The patient says their skin reddens with sun exposure · the referring clinician suspected melanoma · a macroscopic clinical photograph of a skin lesion · a moderate number of moles by the patient's own estimate · a female subject aged 50 · the patient reports a personal history of skin cancer.
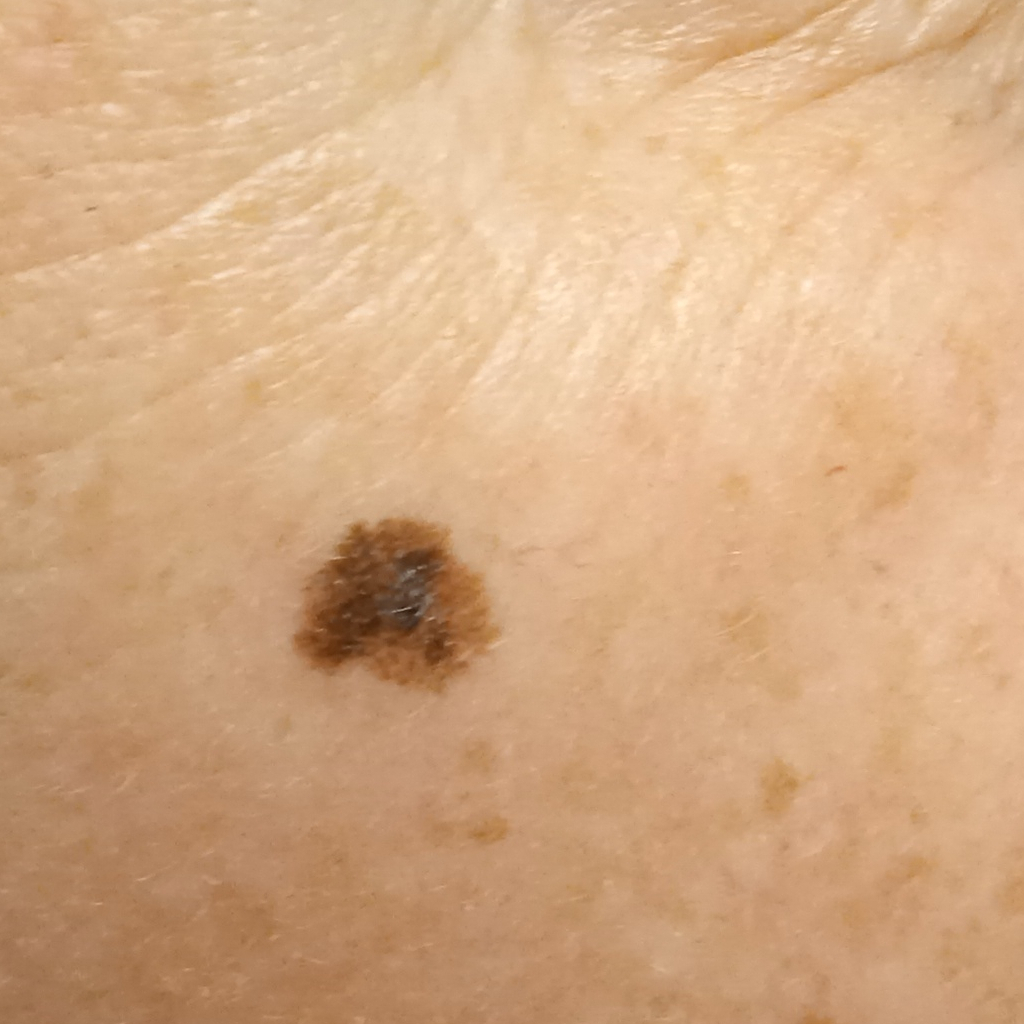anatomic site: the face; size: 7 mm; diagnosis: melanoma (biopsy-proven).